A dermatoscopic image of a skin lesion.
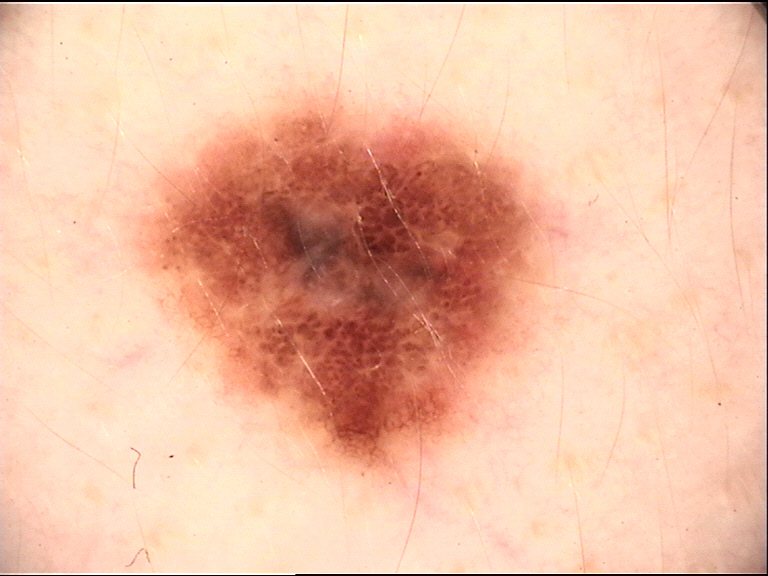Biopsy-confirmed as a melanoma.